FST I · the lesion is associated with burning, pain, bothersome appearance and itching · the patient indicates the lesion is fluid-filled · female patient, age 40–49 · no associated systemic symptoms reported · the patient indicates the condition has been present for three to twelve months · this is a close-up image · the head or neck and arm are involved:
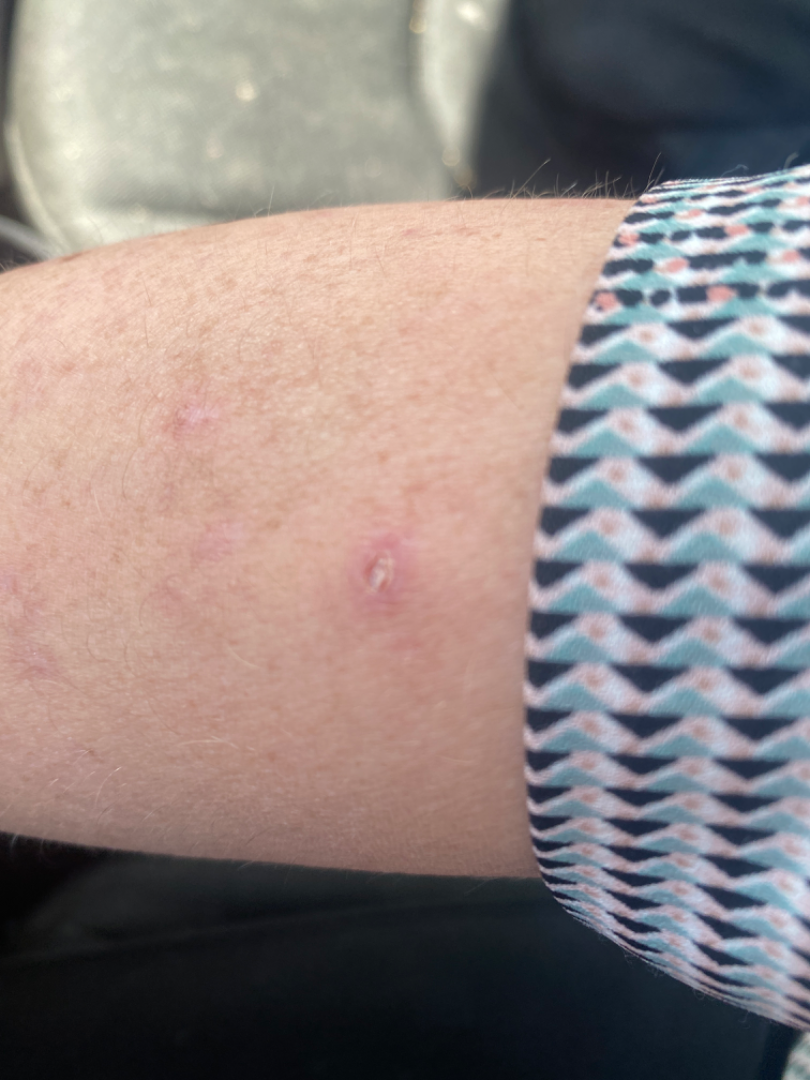Q: What is the dermatologist's impression?
A: favoring Actinic Keratosis